An image taken at a distance. The affected area is the arm. The contributor is 60–69, female.
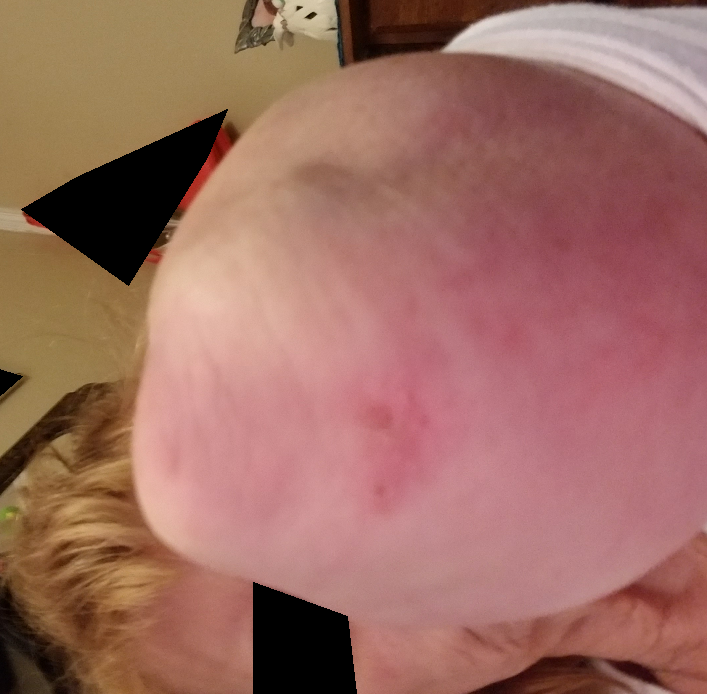Case summary:
* assessment — ungradable on photographic review